The patient says their skin reddens with sun exposure · a macroscopic clinical photograph of a skin lesion · a female patient 59 years old · collected as part of a research study, without a referral diagnosis.
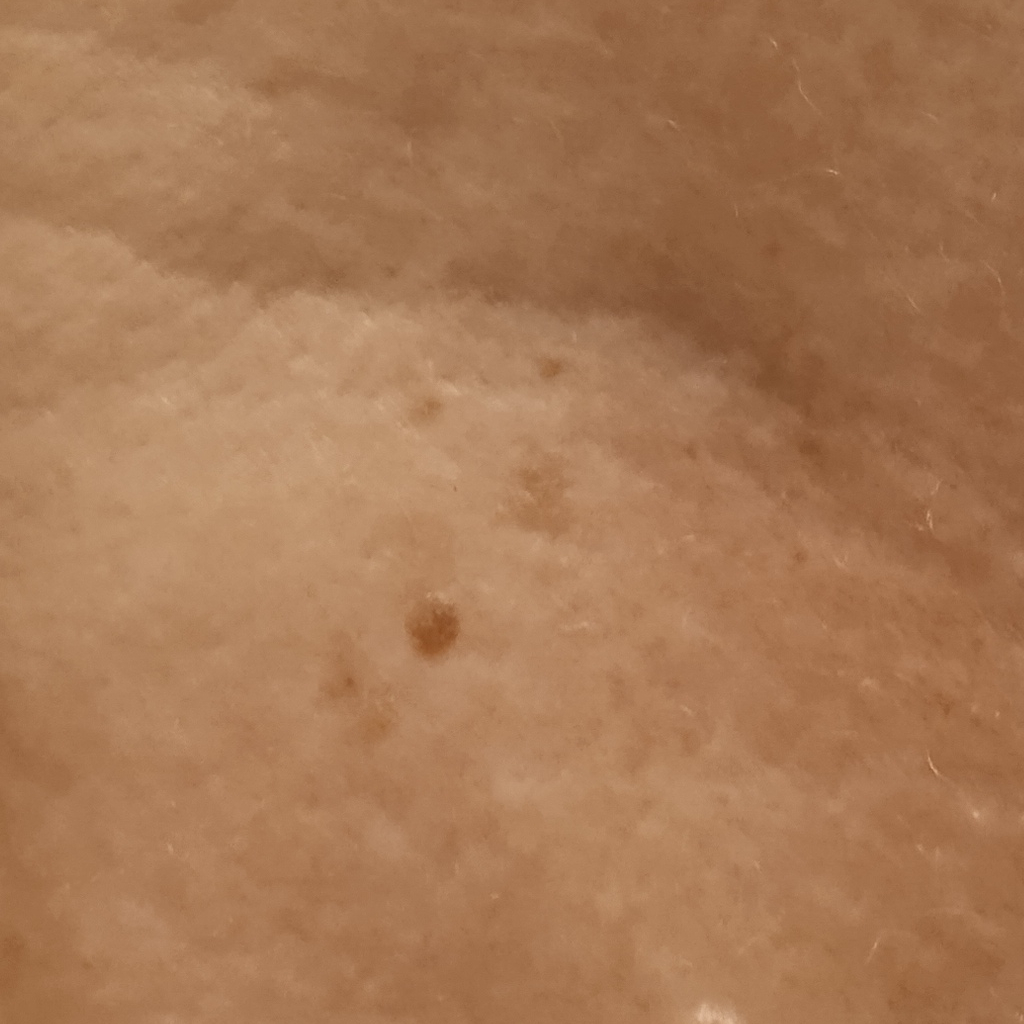Summary:
Located on the torso. The lesion is about 2.2 mm across.
Conclusion:
The diagnostic impression was a seborrheic keratosis.